Fitzpatrick skin type III; a clinical close-up photograph of a skin lesion; the chart notes pesticide exposure and alcohol use: 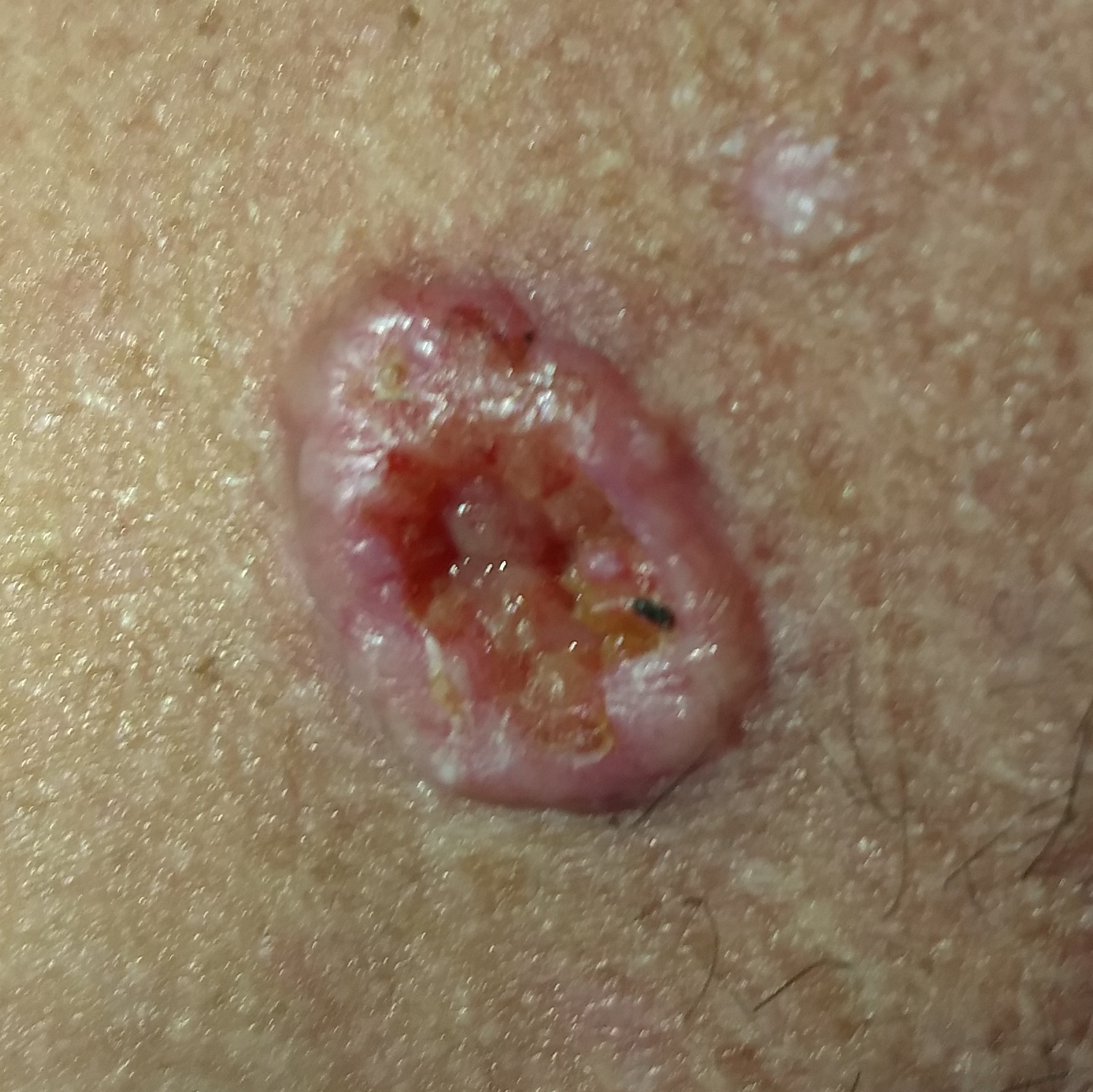{"lesion_location": "the neck", "lesion_size": {"diameter_1_mm": 20.0, "diameter_2_mm": 14.0}, "symptoms": {"present": ["growth", "elevation", "bleeding", "itching", "pain"]}, "diagnosis": {"name": "basal cell carcinoma", "code": "BCC", "malignancy": "malignant", "confirmation": "histopathology"}}